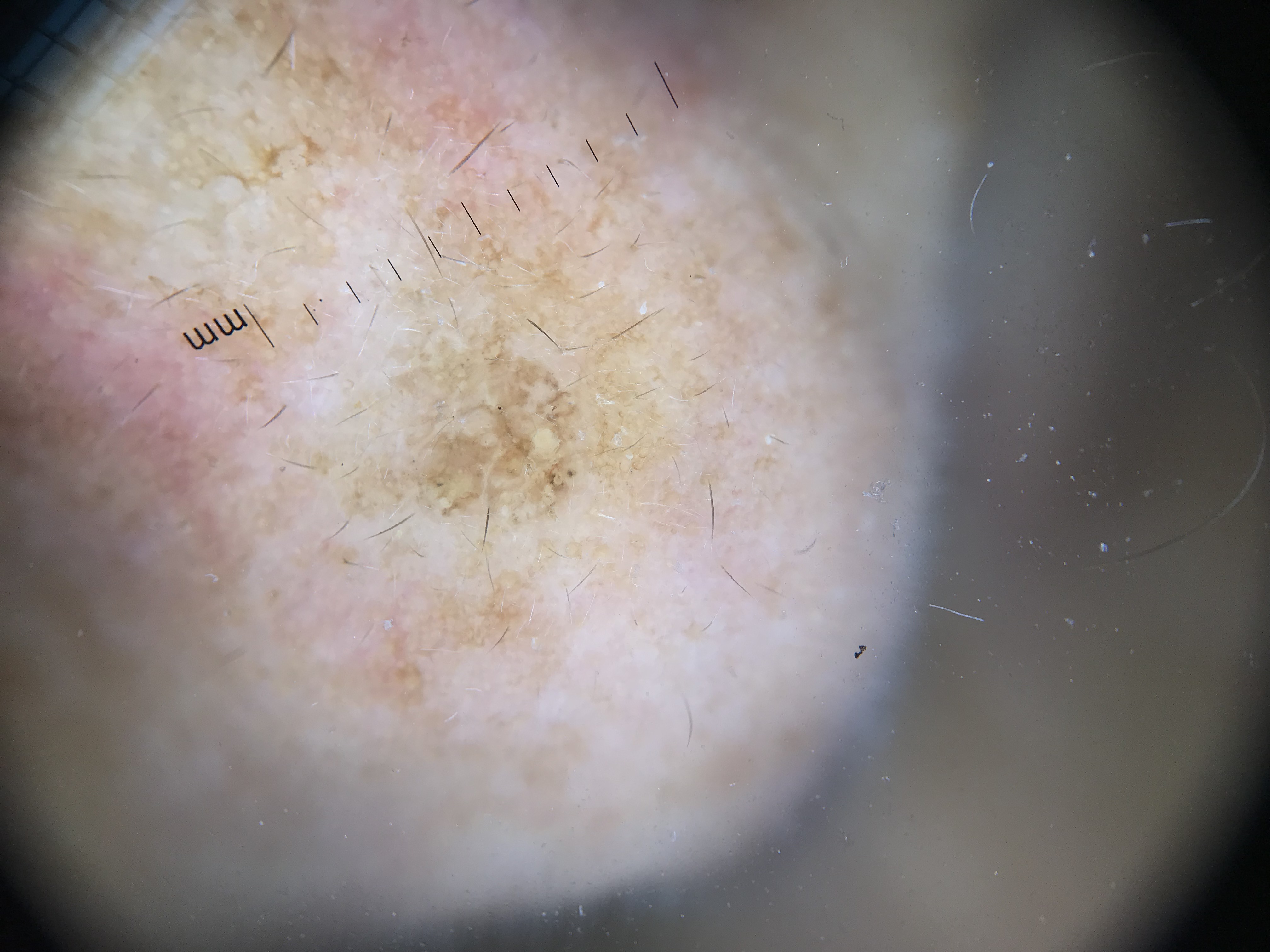class — seborrheic keratosis (expert consensus)